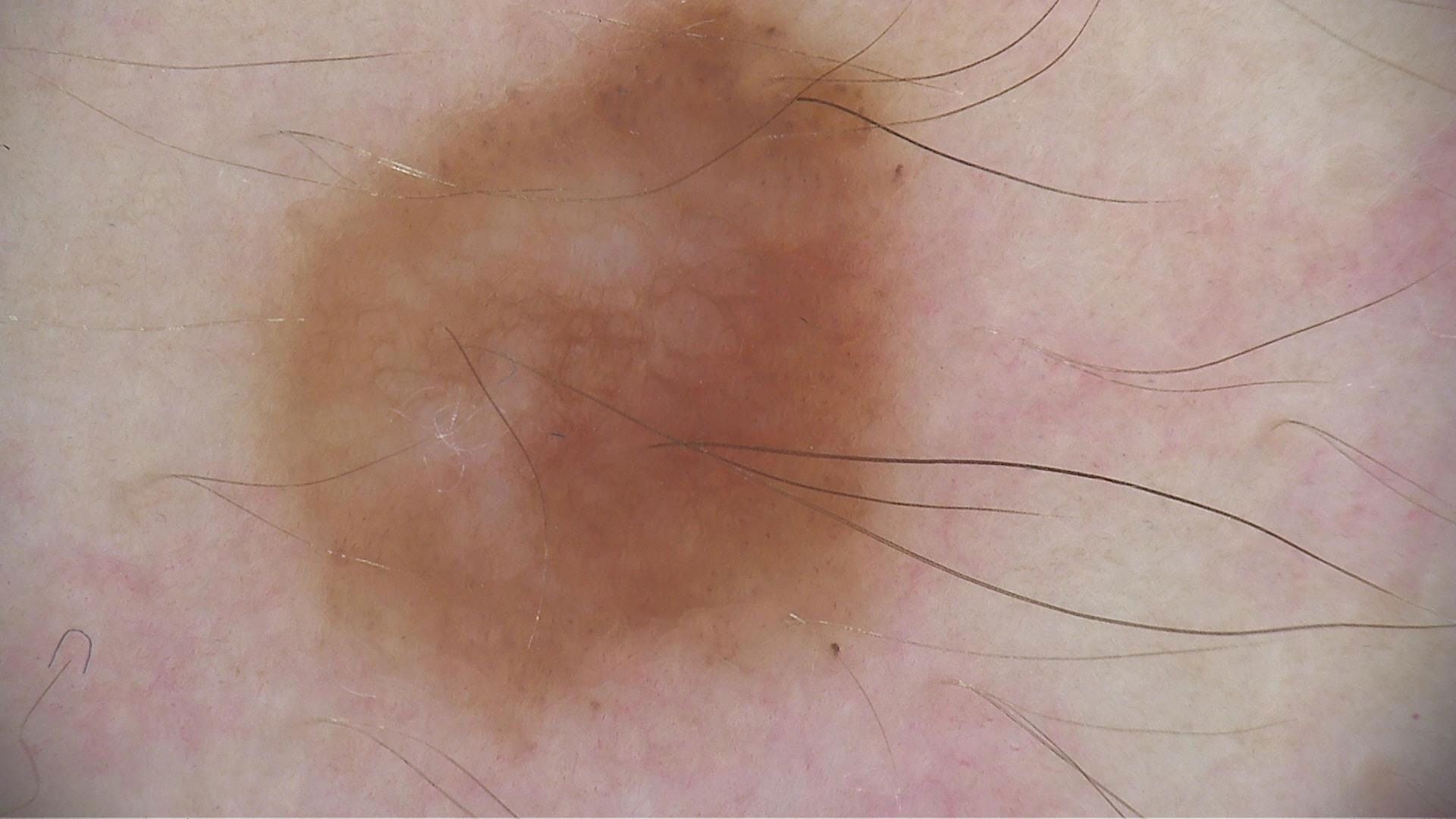The diagnosis was a dysplastic junctional nevus.